A dermoscopic close-up of a skin lesion · per the chart, a prior melanoma · skin type II: 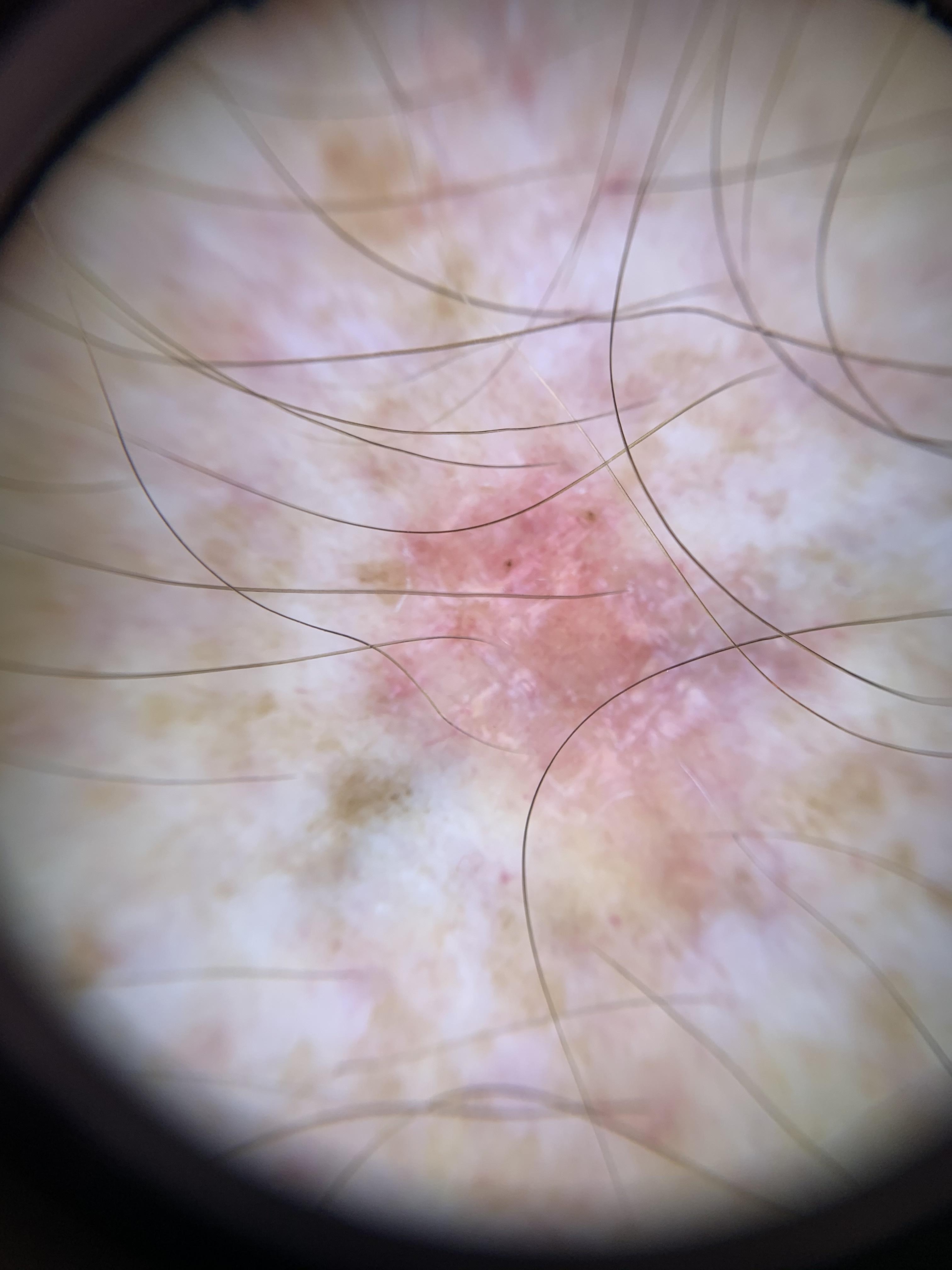The lesion is on a lower extremity. Biopsy-confirmed as a malignant, adnexal lesion — a basal cell carcinoma.